The arm is involved; the photograph is a close-up of the affected area — 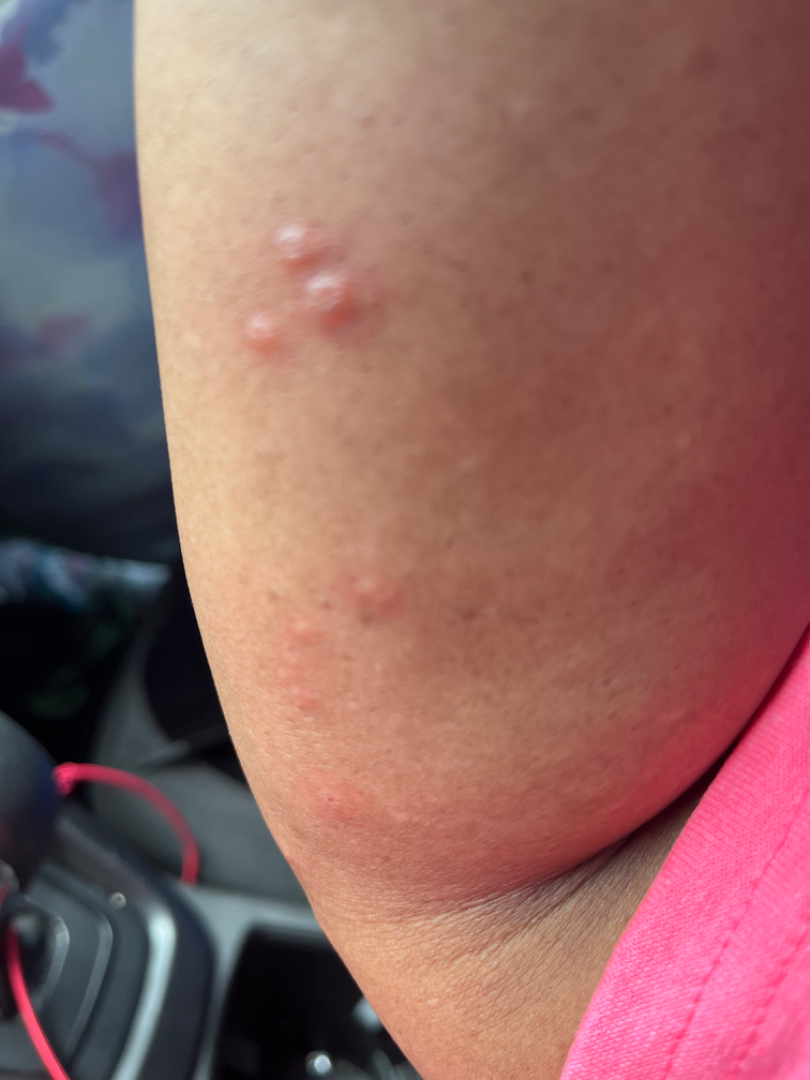Findings:
– diagnostic considerations — reviewed remotely by one dermatologist: in keeping with Molluscum Contagiosum